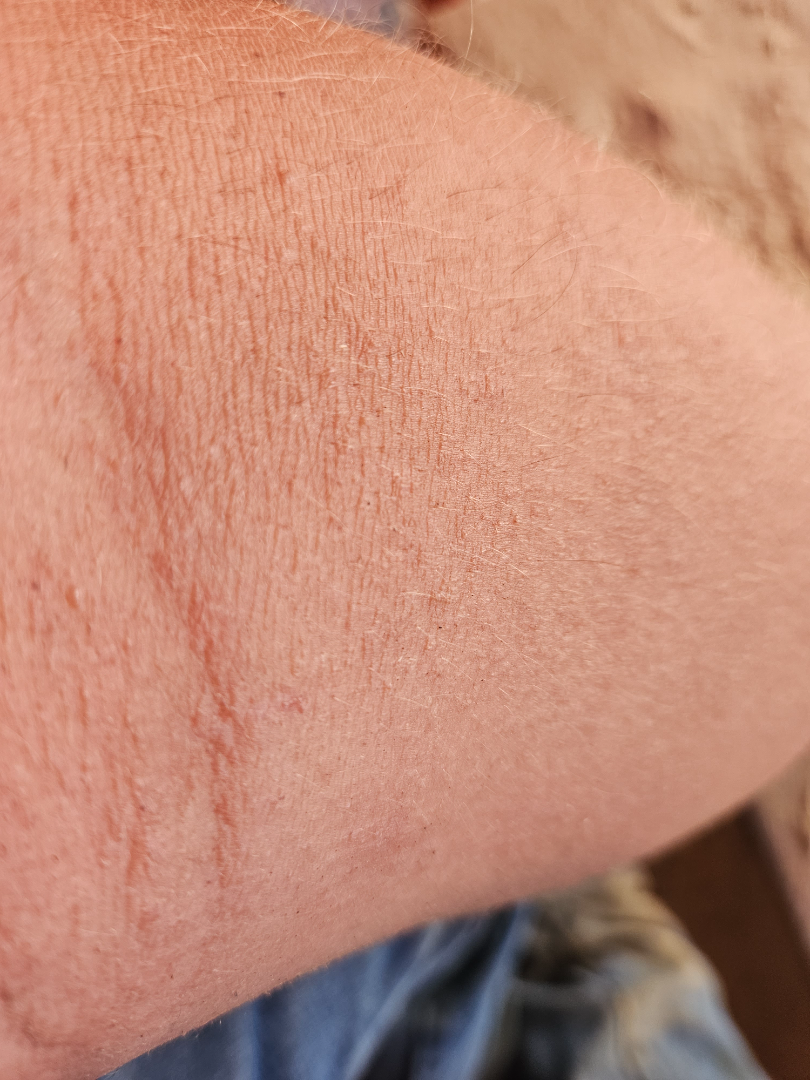The affected area is the arm. This image was taken at an angle. On remote review of the image, Allergic Contact Dermatitis (considered); Xerosis (considered); Eczema (considered); Sunburn (unlikely); Keratosis pilaris (unlikely).